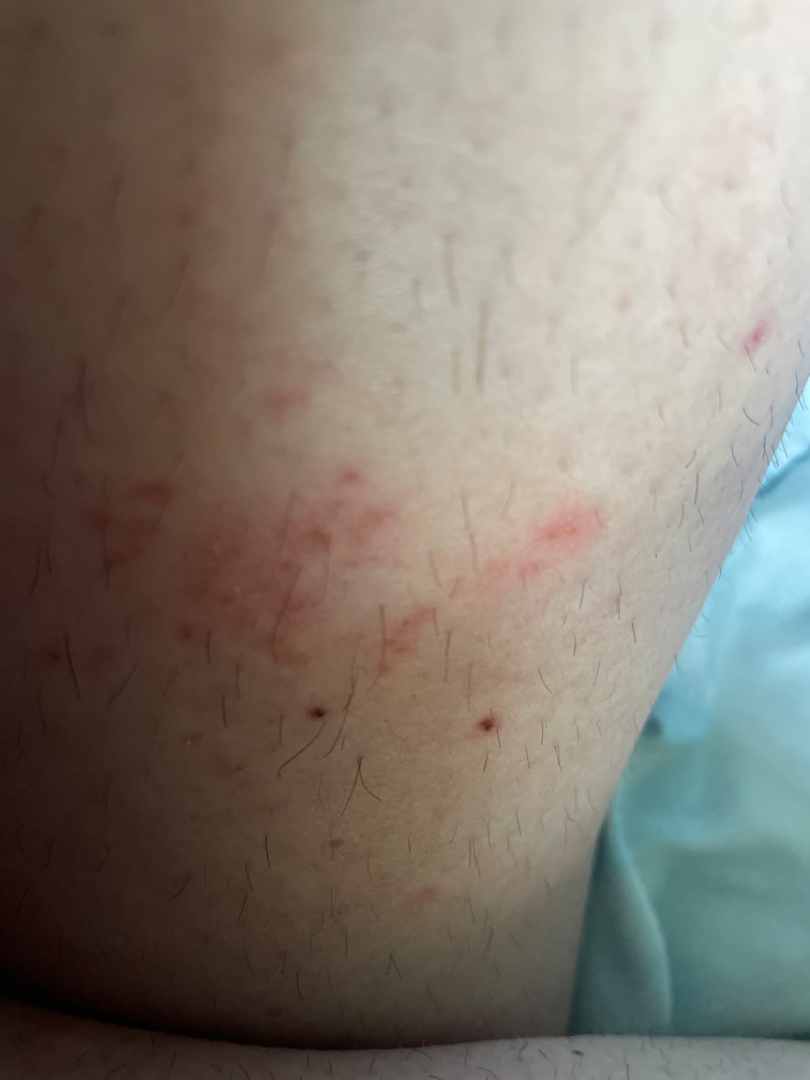The dermatologist could not determine a likely condition from the photograph alone.